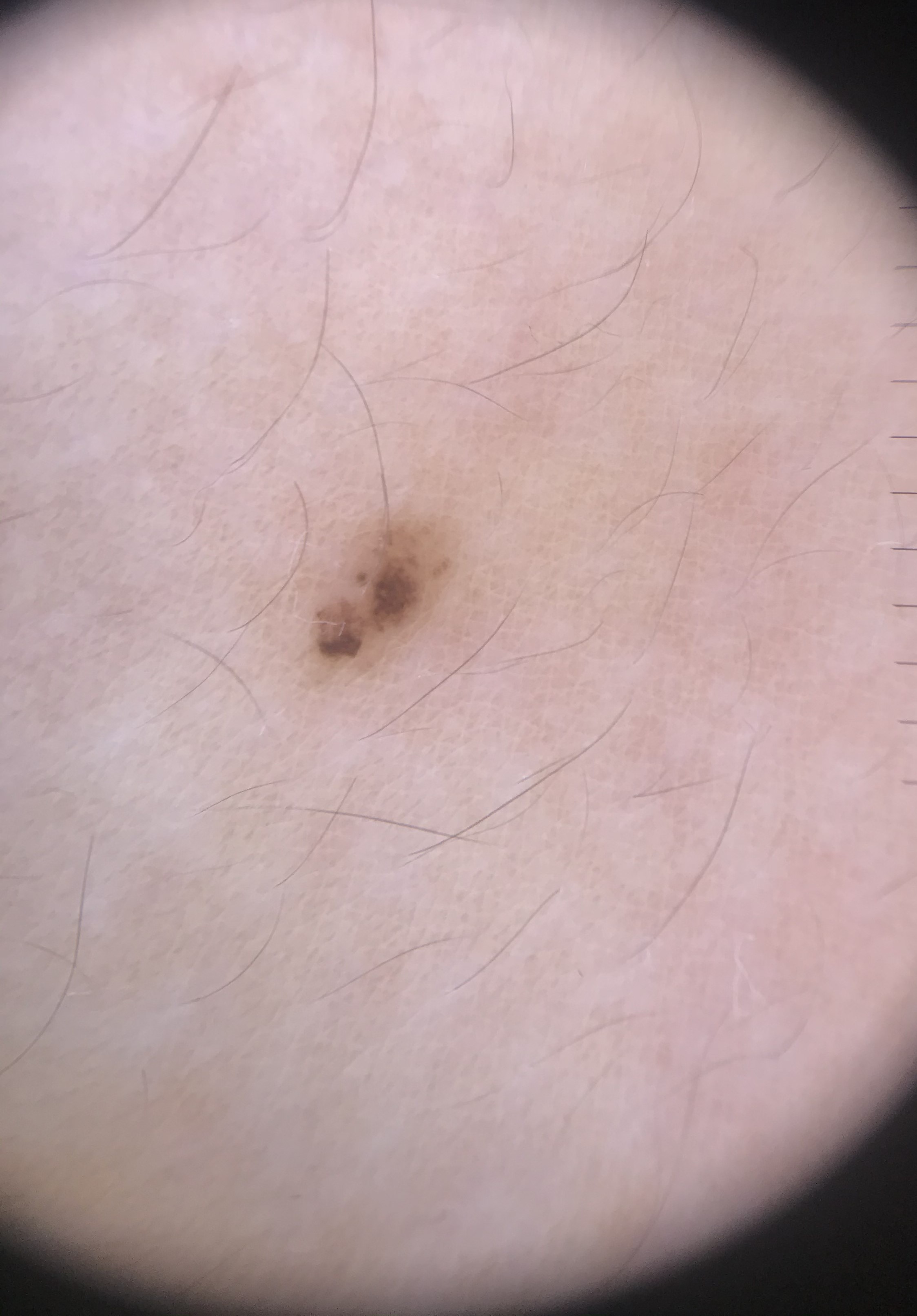A skin lesion imaged with a dermatoscope. Classified as a banal lesion — a compound nevus.